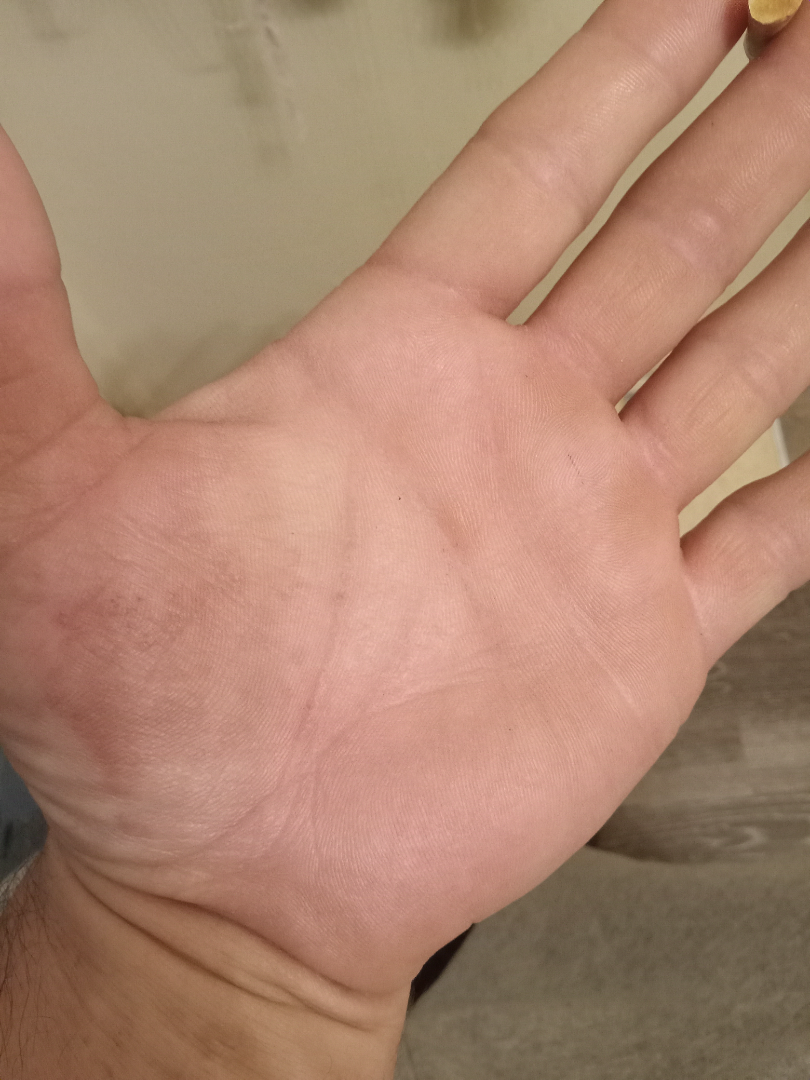photo taken: close-up
assessment: Eczema and Psoriasis were each considered, in no particular order